A dermatoscopic image of a skin lesion: 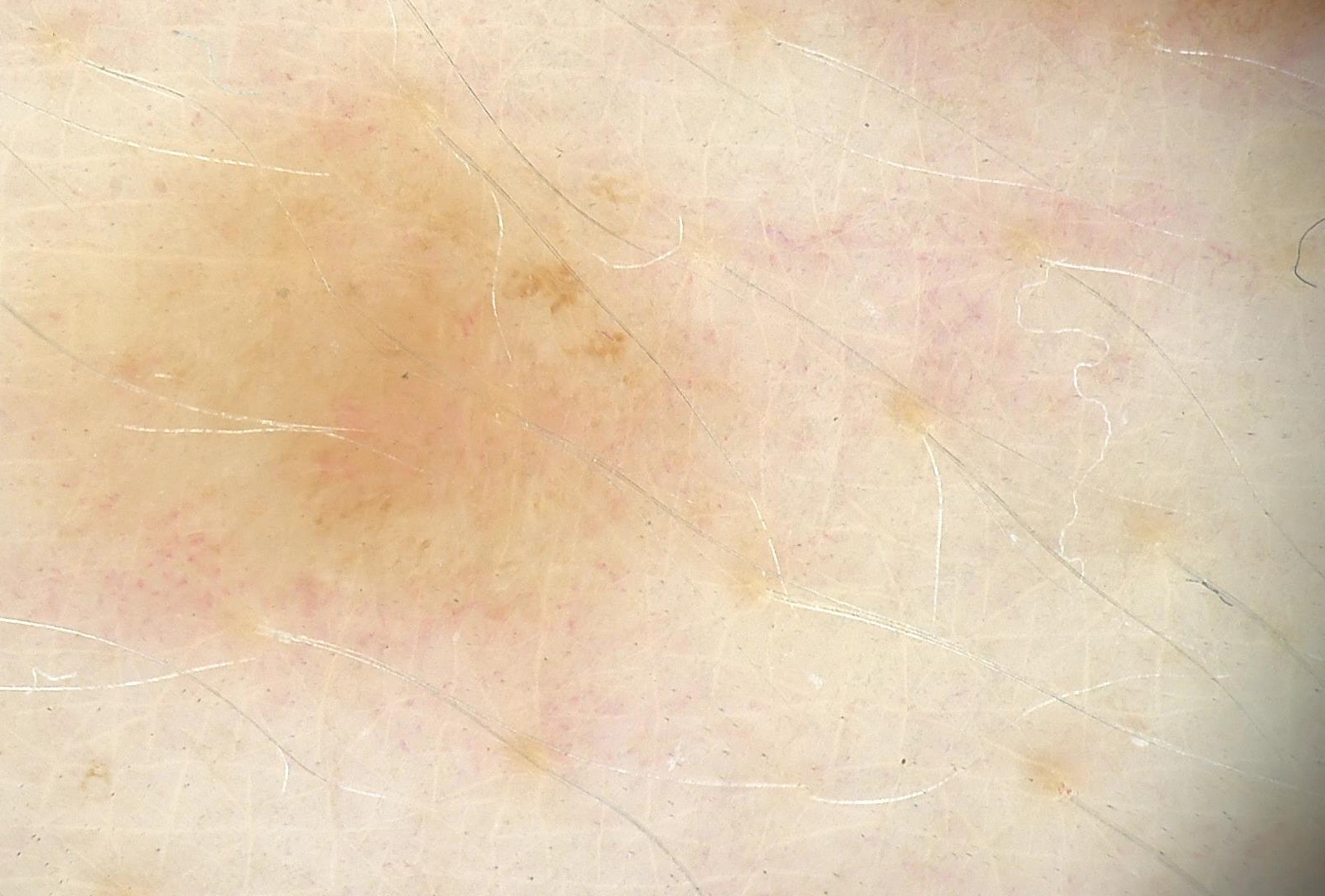Case:
• diagnosis — dysplastic junctional nevus (expert consensus)